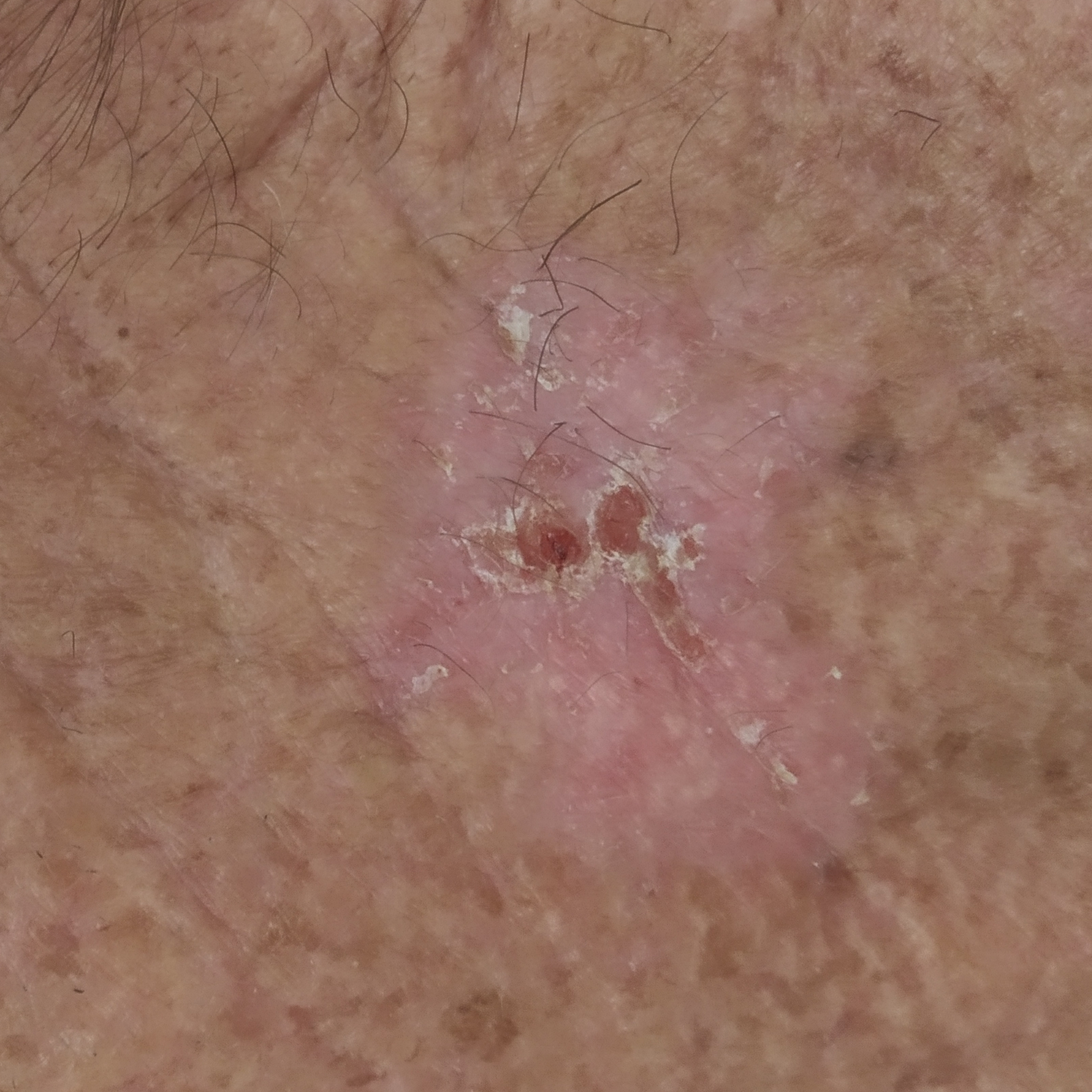Q: Skin phototype?
A: II
Q: What are the relevant risk factors?
A: pesticide exposure, no prior skin cancer (patient or family), no tobacco use
Q: Who is the patient?
A: male, 65 years old
Q: Where on the body is the lesion?
A: the neck
Q: Lesion size?
A: 30 × 27 mm
Q: What does the patient describe?
A: elevation, itching, bleeding / no pain
Q: What is this lesion?
A: basal cell carcinoma (biopsy-proven)